The lesion involves the arm. Close-up view — 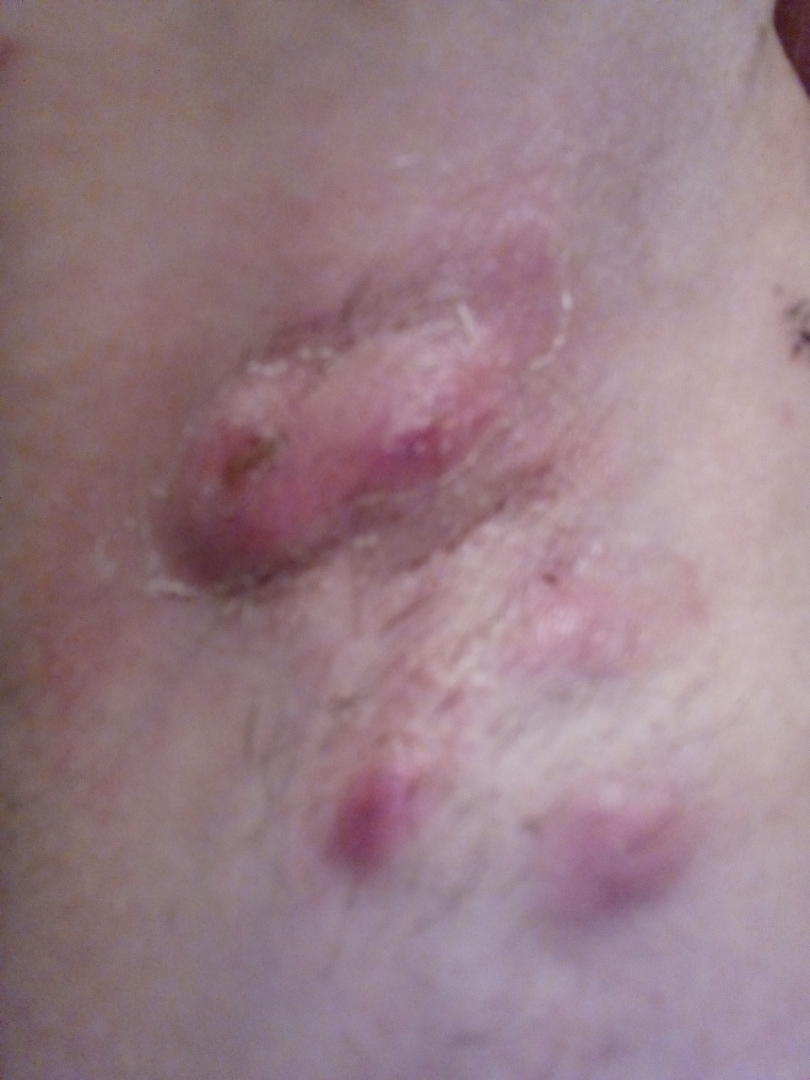Clinical context: The patient described the issue as a hair problem. The patient also reports mouth sores. Present for less than one week. The lesion is associated with pain, itching and enlargement. The lesion is described as fluid-filled and raised or bumpy. Assessment: On remote dermatologist review: the impression on review was Hidradenitis.